Located on the arm, head or neck and front of the torso; an image taken at a distance: 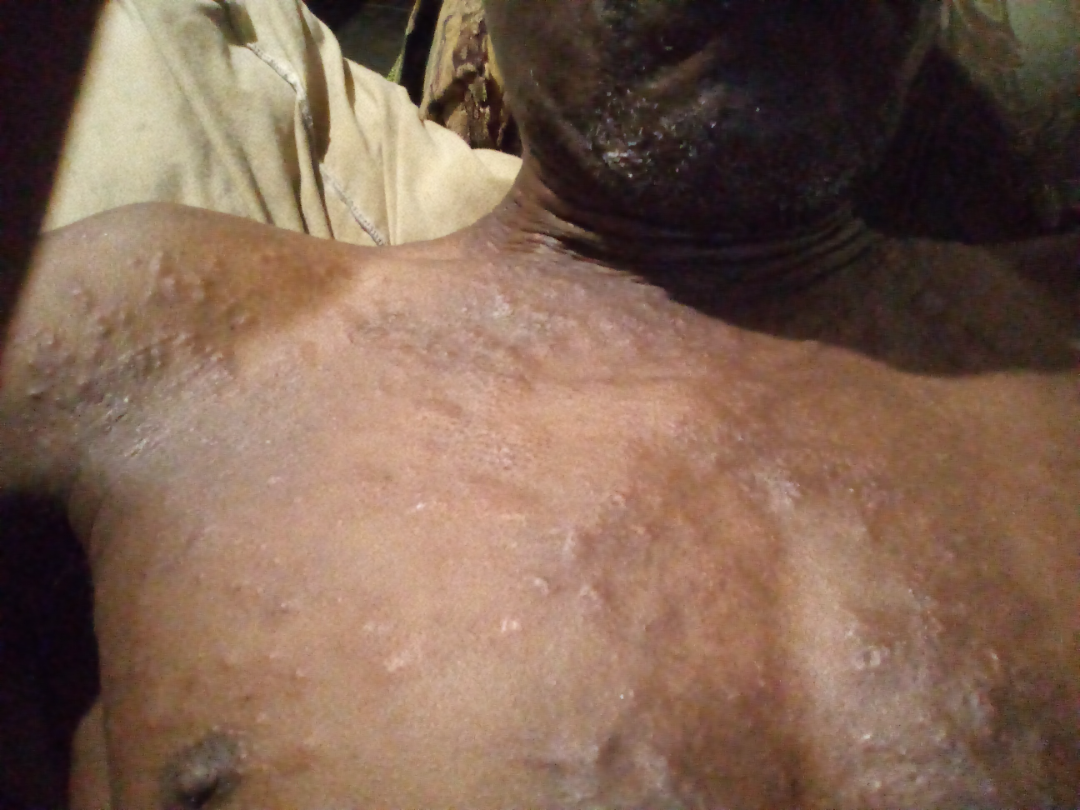Diagnostic features were not clearly distinguishable in this photograph.